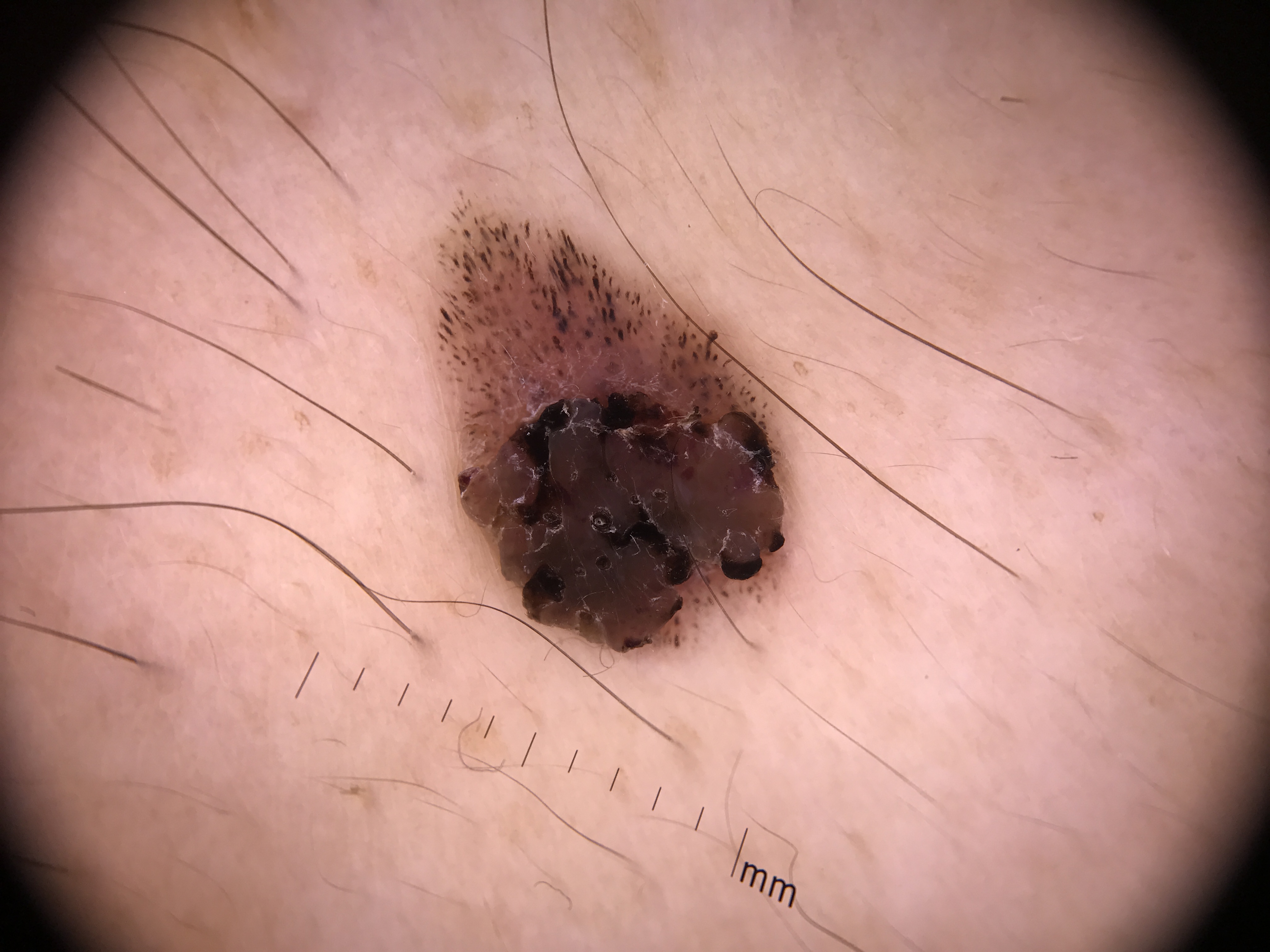Classified as a congenital dysplastic compound nevus.